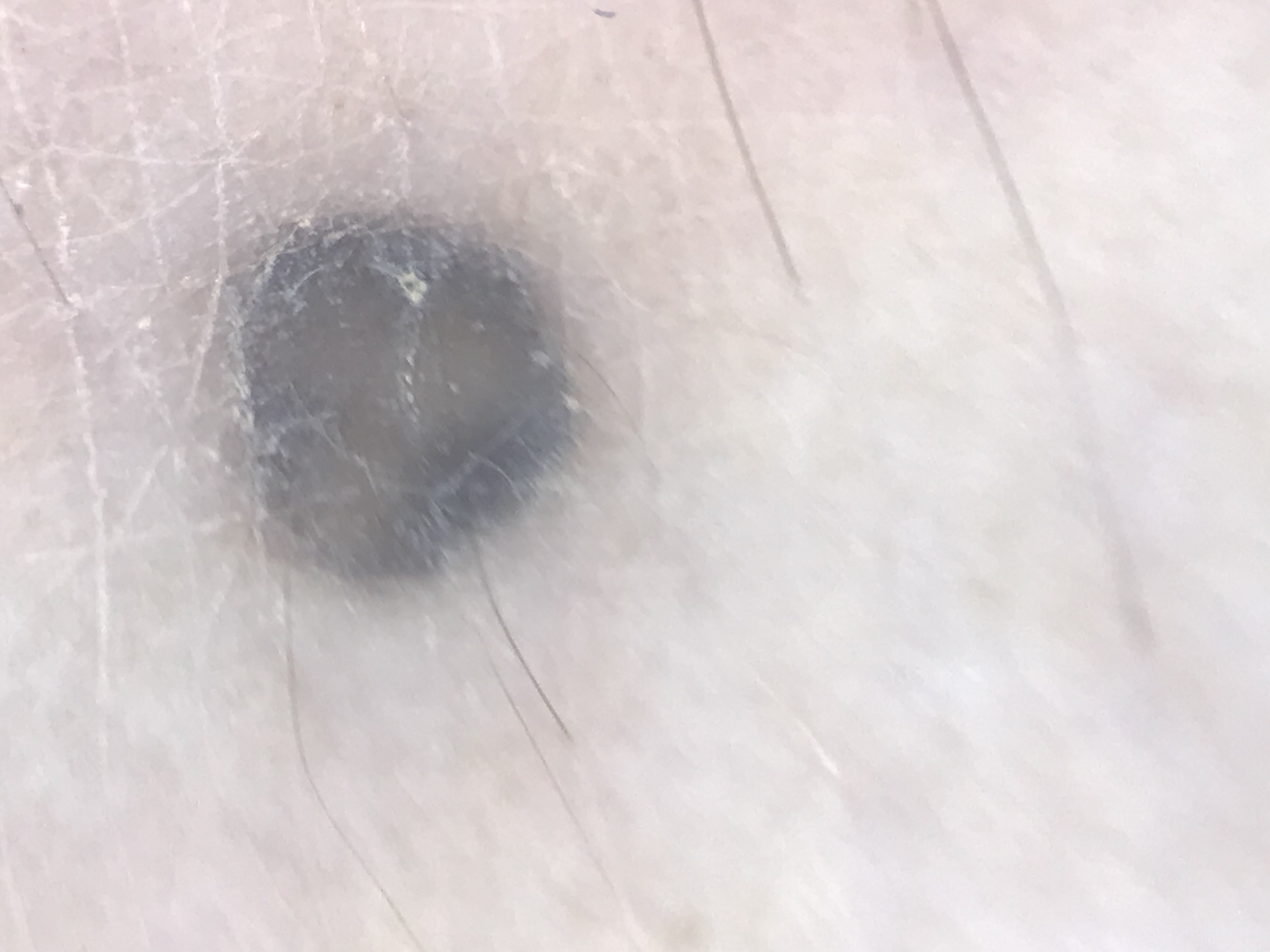The morphology is that of a dermal, banal lesion.
The diagnosis was a blue nevus.